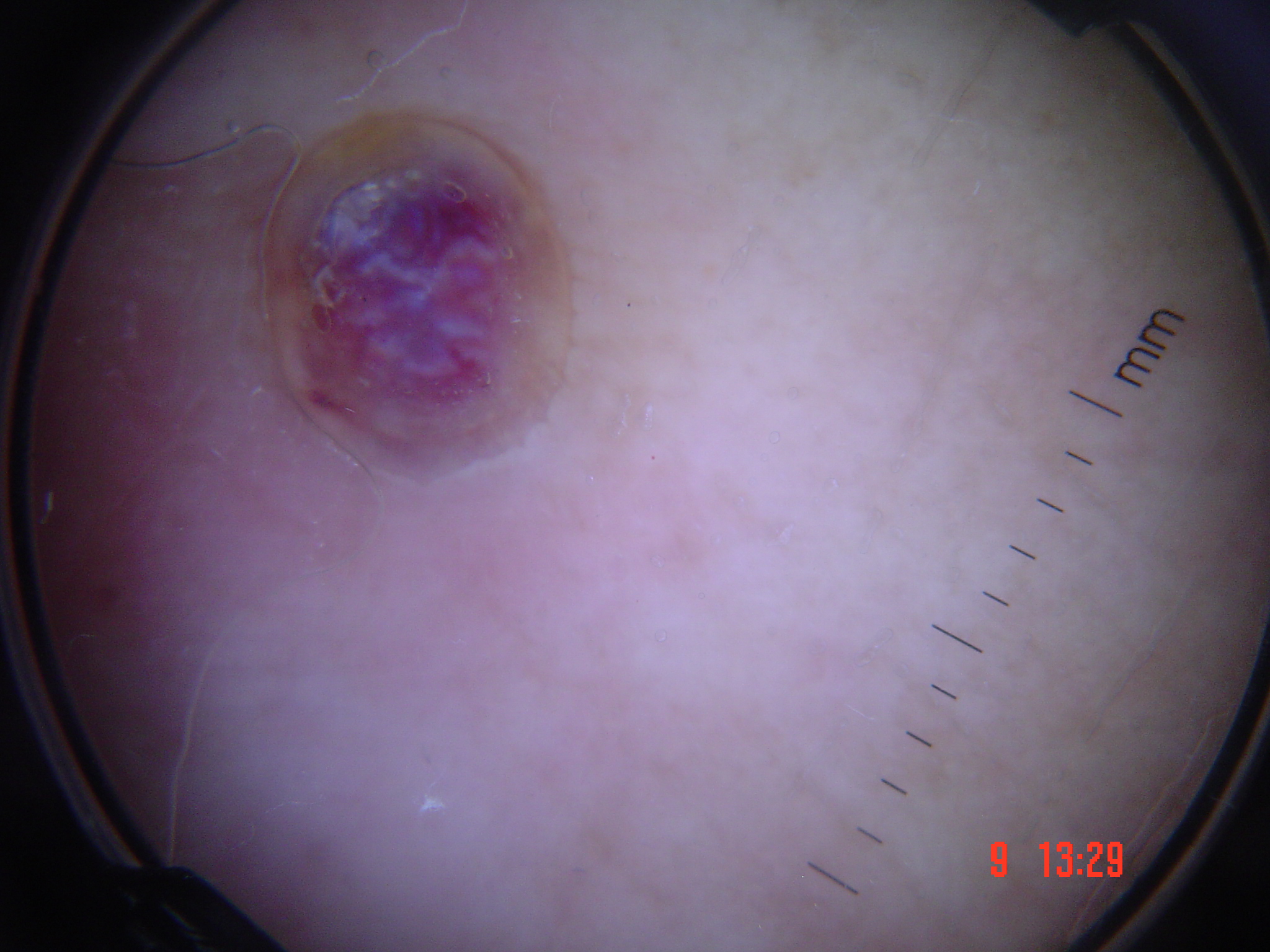image = dermatoscopy; class = Kaposi sarcoma (biopsy-proven).